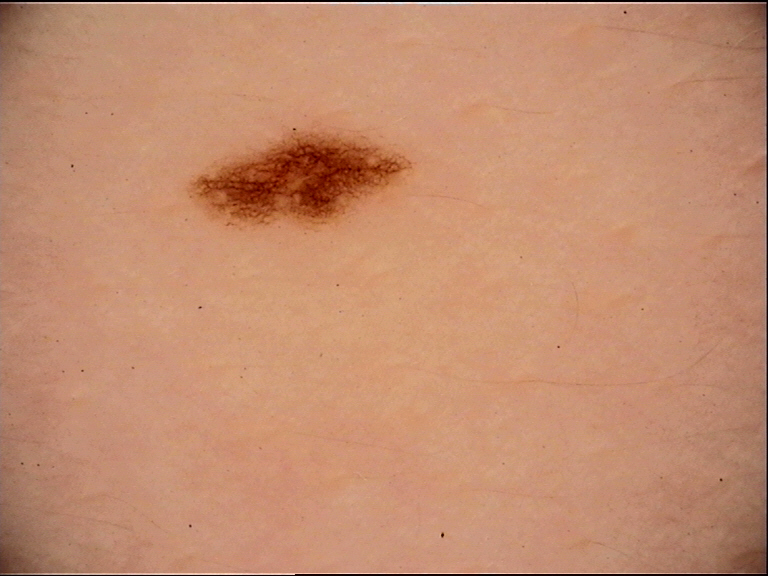image=dermatoscopy | diagnostic label=dysplastic junctional nevus (expert consensus).